A dermoscopic close-up of a skin lesion, a male subject aged approximately 70 — 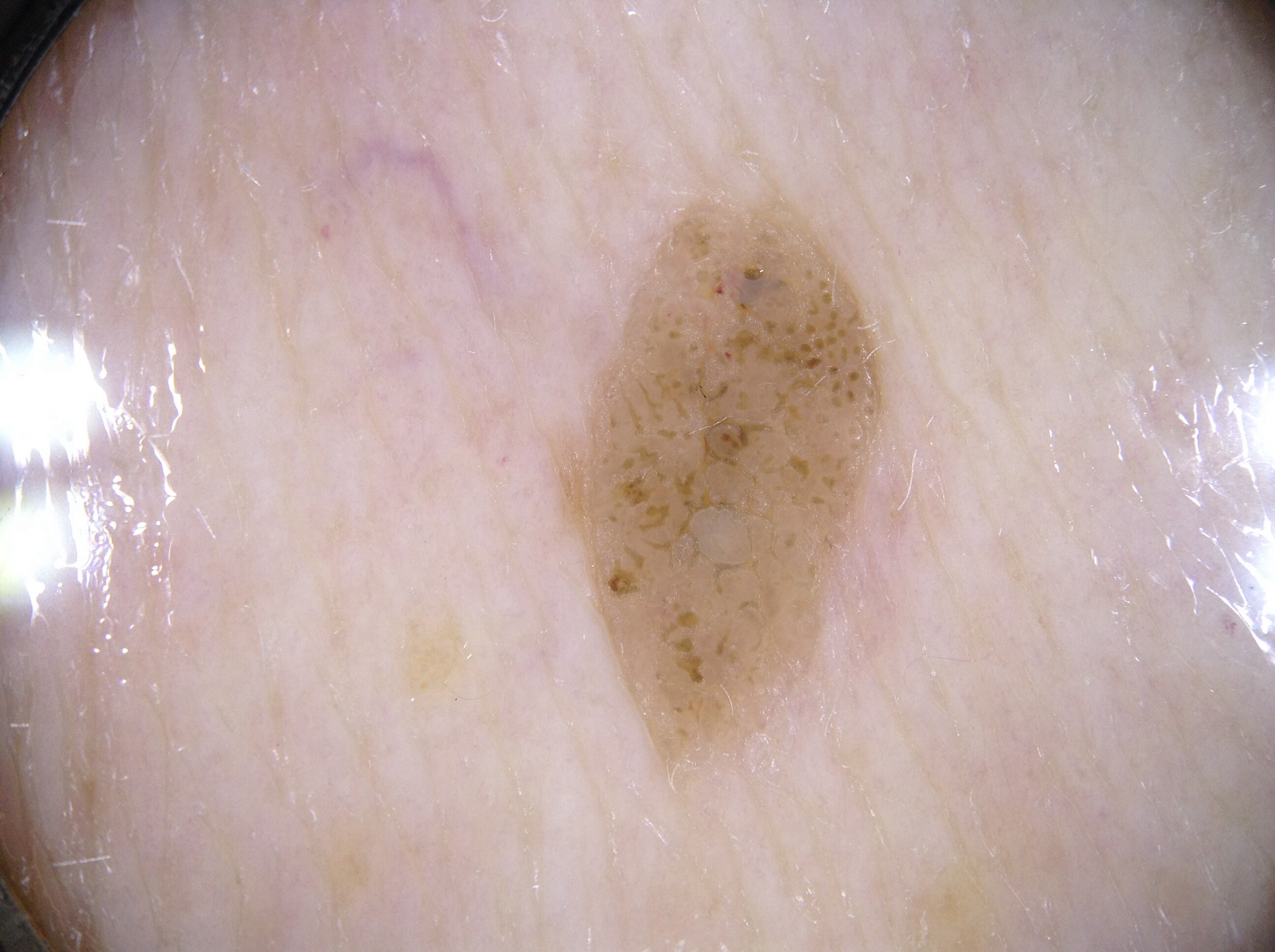<lesion>
<dermoscopic_features>
  <present/>
  <absent>milia-like cysts, negative network, pigment network, streaks</absent>
</dermoscopic_features>
<lesion_location>
  <bbox_xyxy>542, 168, 899, 794</bbox_xyxy>
</lesion_location>
<diagnosis>
  <name>seborrheic keratosis</name>
  <malignancy>benign</malignancy>
  <lineage>keratinocytic</lineage>
  <provenance>clinical</provenance>
</diagnosis>
</lesion>